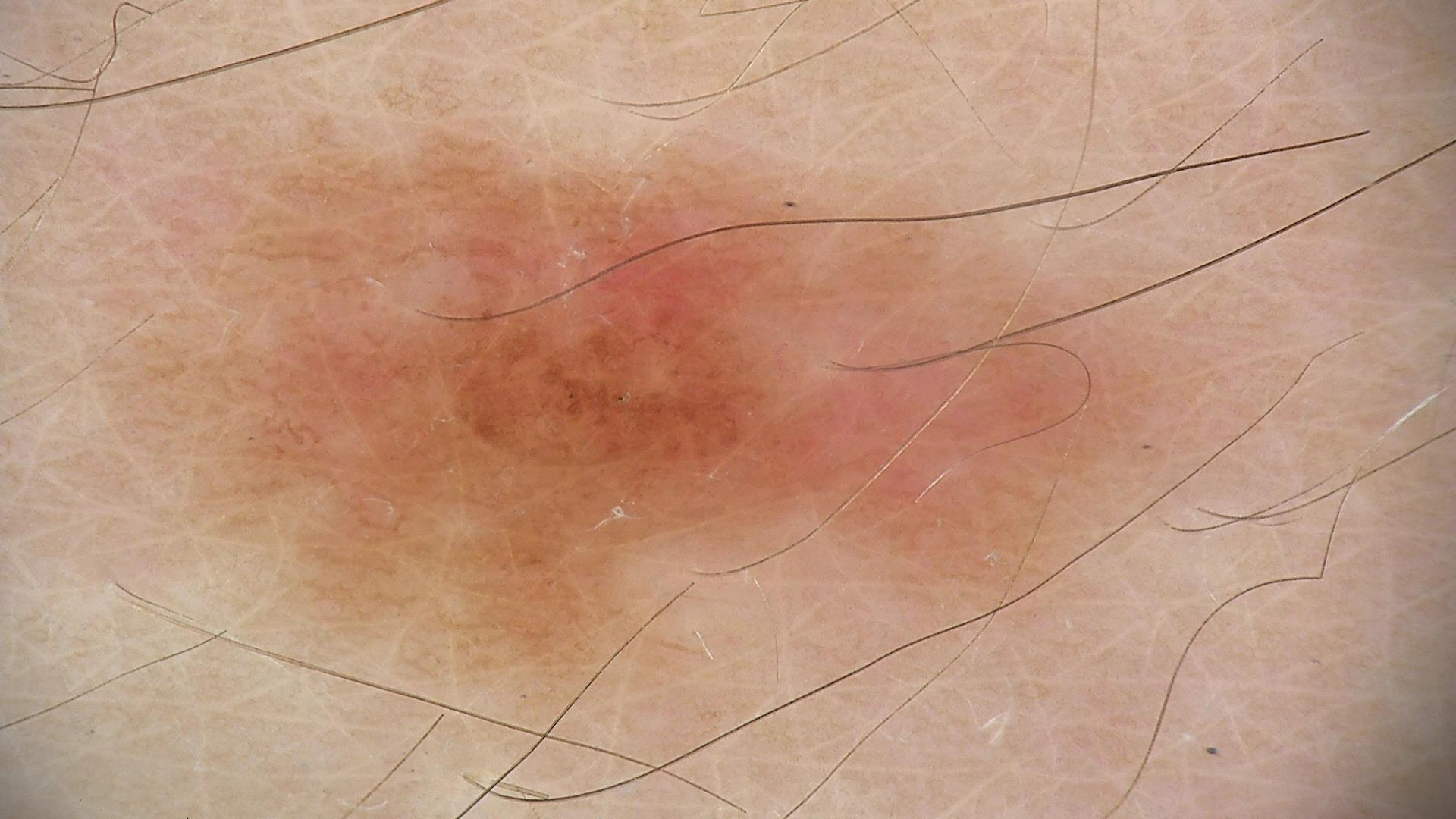image type = dermatoscopy; subtype = banal; diagnostic label = compound nevus (expert consensus).